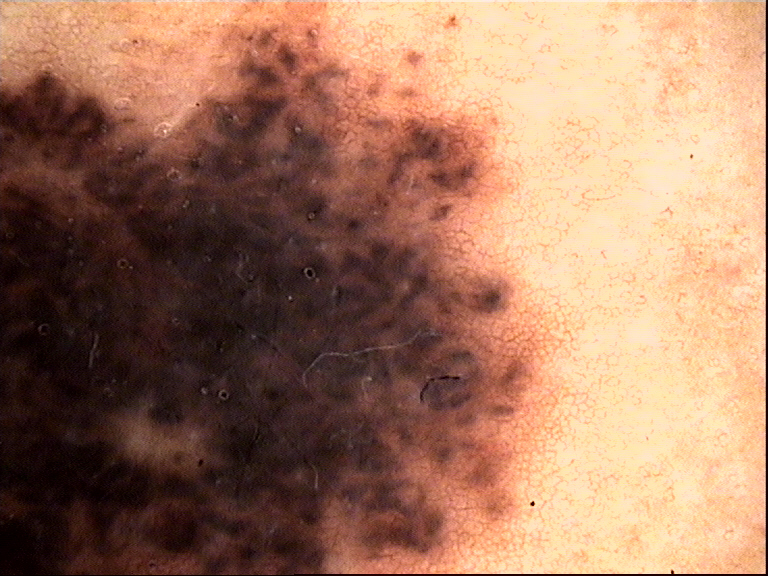lesion type=banal | diagnostic label=congenital compound nevus (expert consensus).